A dermoscopic photograph of a skin lesion.
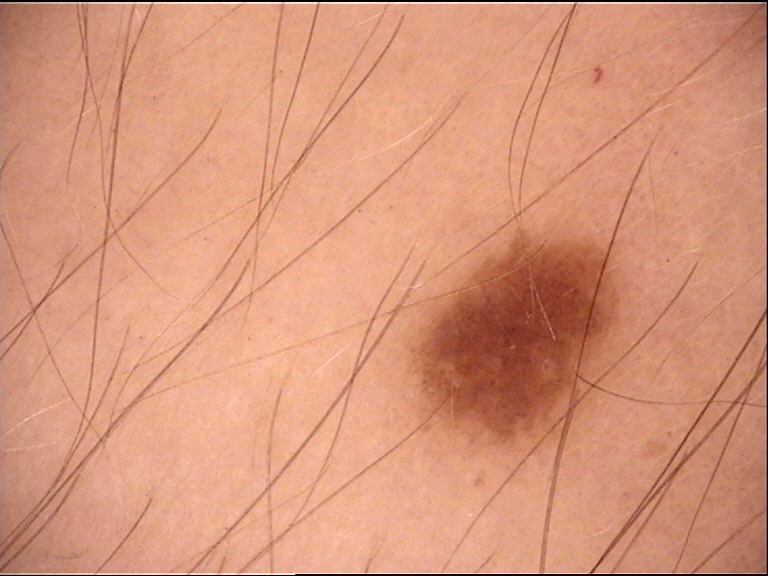The architecture is that of a banal lesion.
The diagnostic label was a junctional nevus.